The photo was captured at an angle · the leg, head or neck and top or side of the foot are involved:
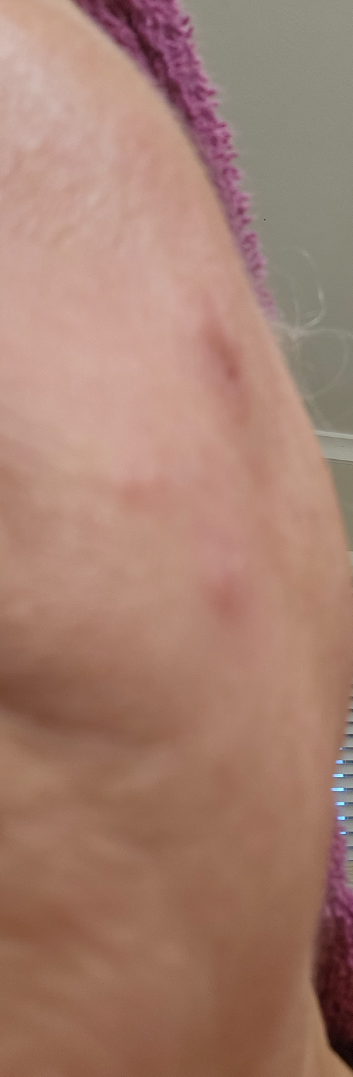Assessment: Reviewed remotely by one dermatologist: the differential, in no particular order, includes Allergic Contact Dermatitis and Irritant Contact Dermatitis.